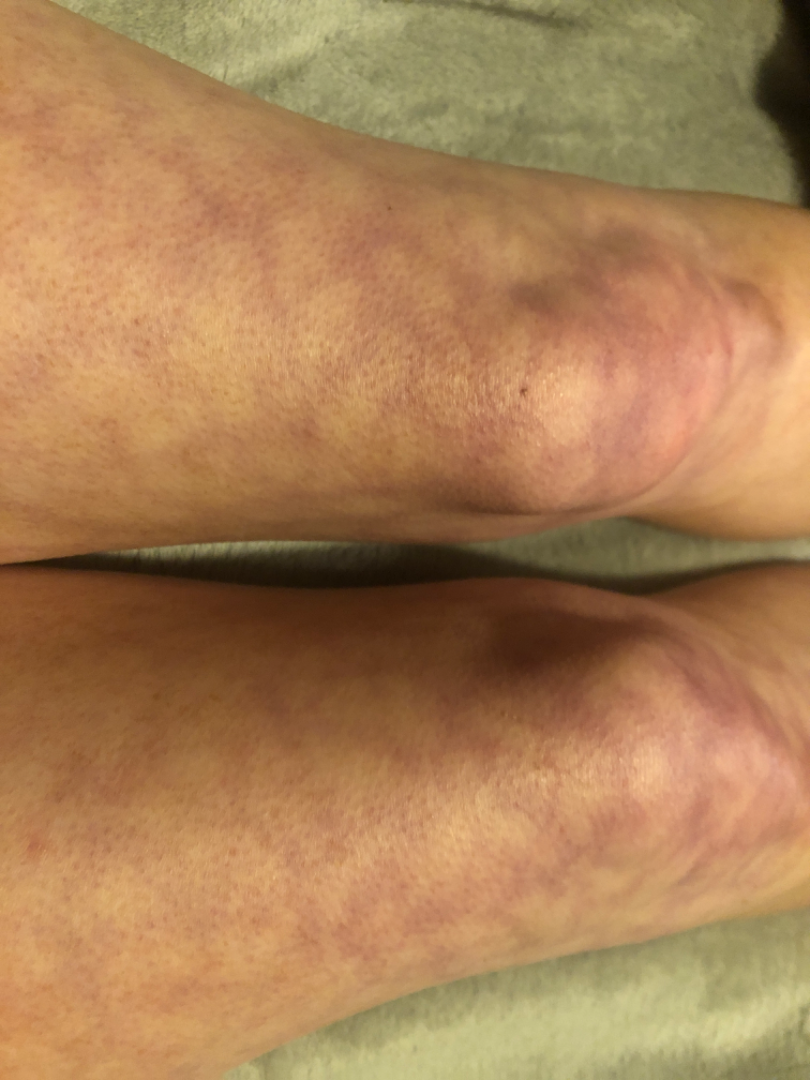The lesion is associated with bothersome appearance. The patient reports the lesion is flat. A close-up photograph. Female contributor, age 30–39. The affected area is the leg. Livedo reticularis and Erythema ab igne were considered with similar weight.